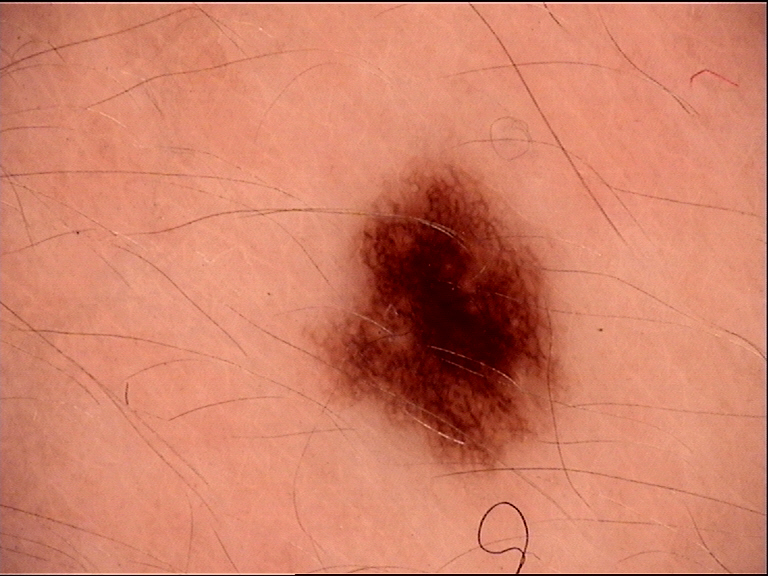A dermoscopic photograph of a skin lesion.
The diagnostic label was a dysplastic junctional nevus.